Reported duration is one to four weeks, the patient considered this a rash, close-up view, texture is reported as fluid-filled and raised or bumpy, located on the arm, symptoms reported: enlargement and itching — 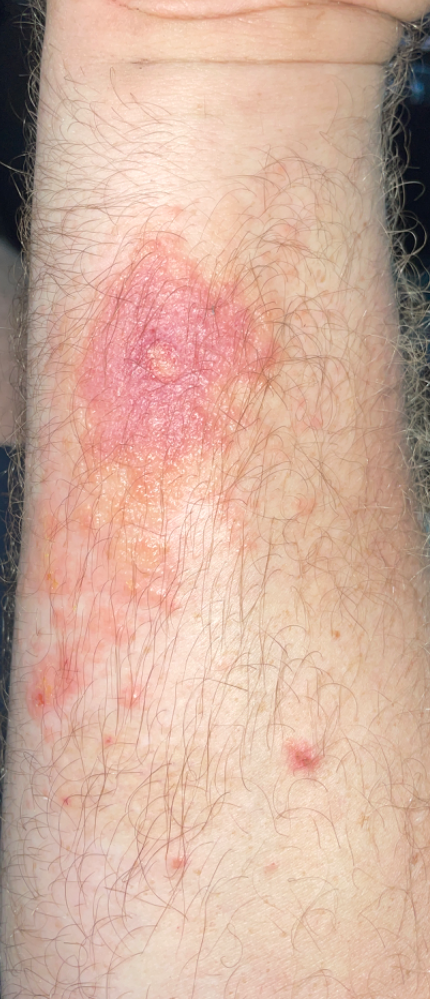Notes:
- differential · in keeping with Allergic Contact Dermatitis